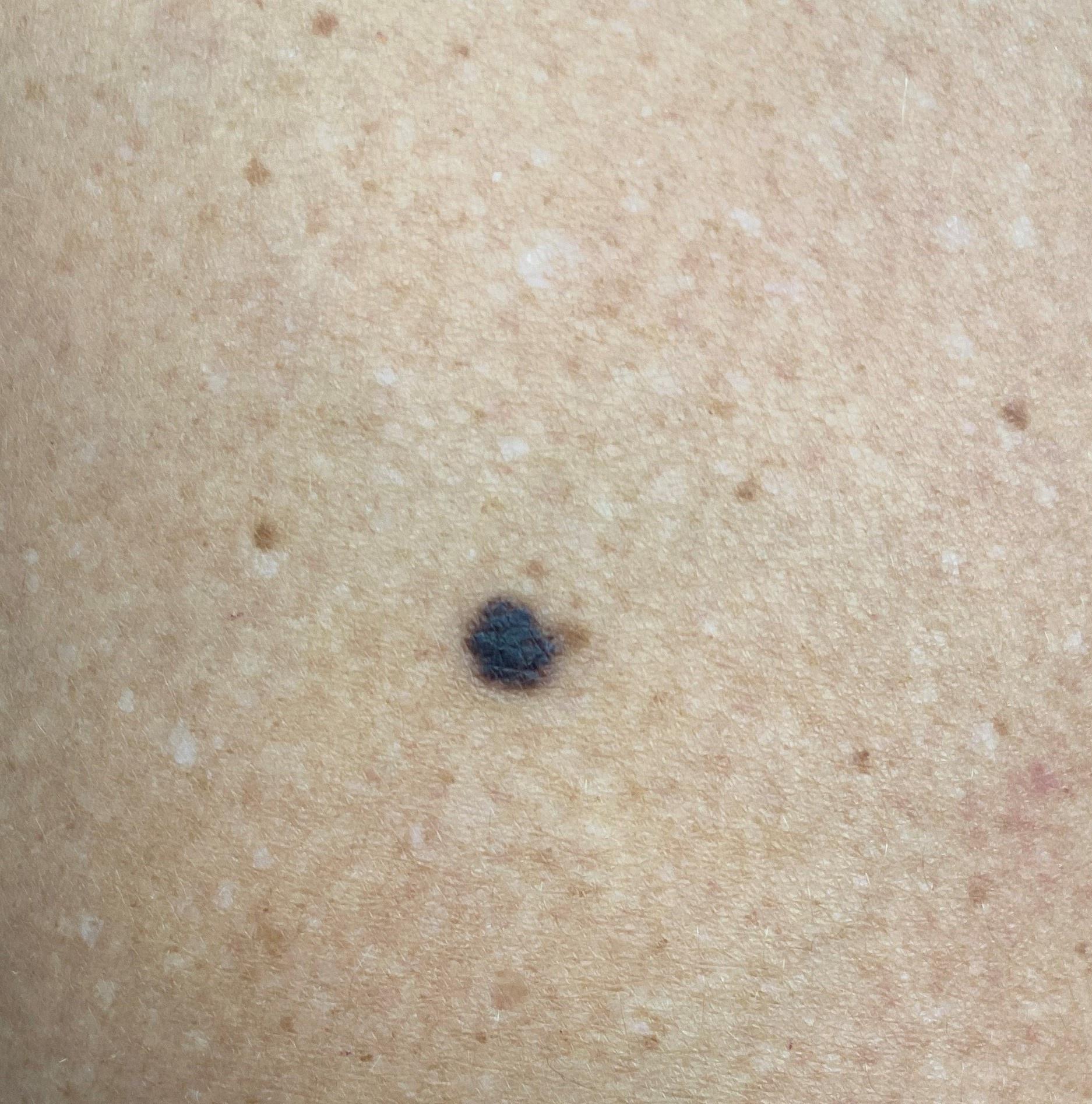A clinical photograph showing a skin lesion in context.
Fitzpatrick skin type II.
A female subject approximately 45 years of age.
The lesion involves a lower extremity.
The biopsy diagnosis was a lesion of melanocytic origin — a nevus.